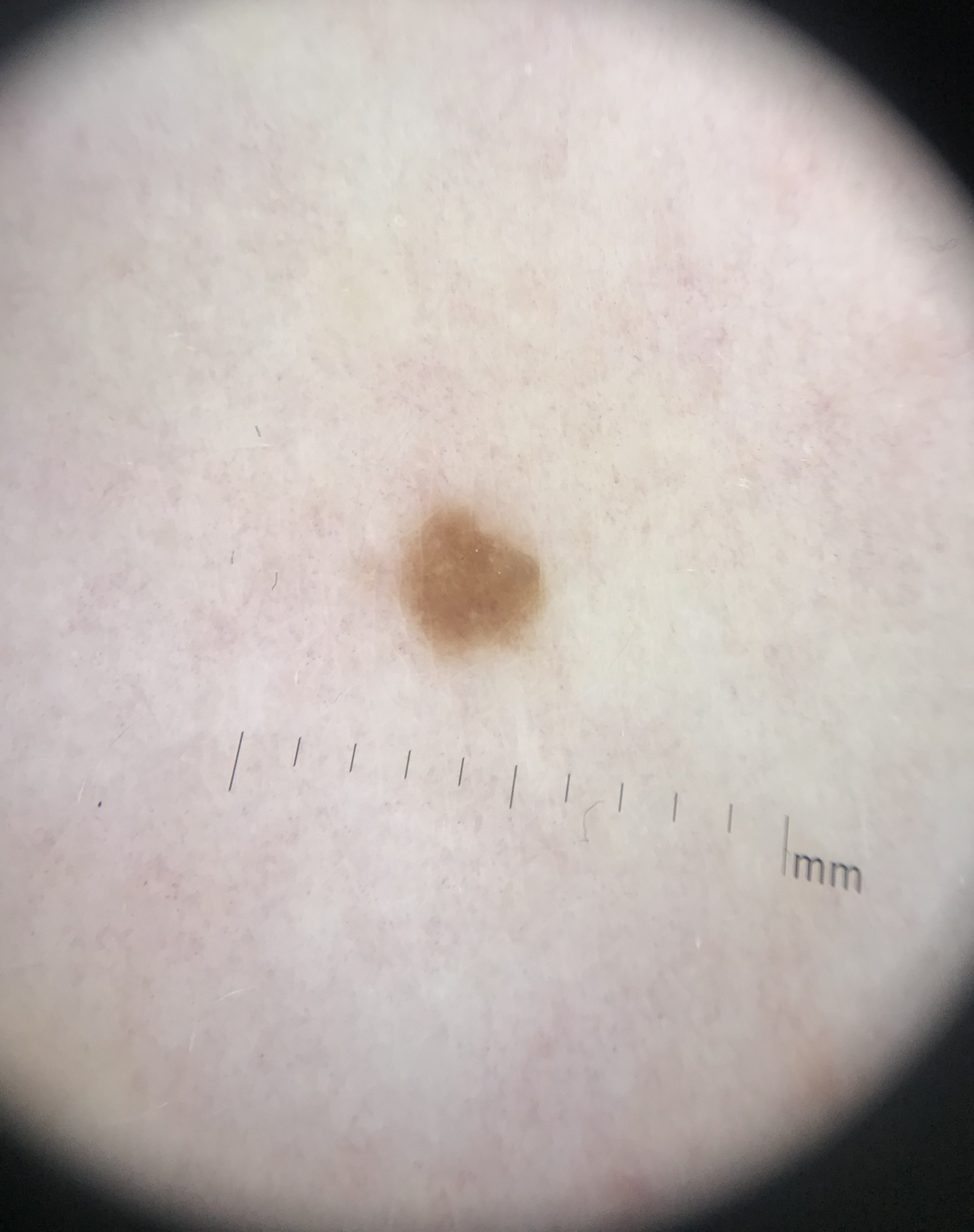A dermoscopic photograph of a skin lesion.
The morphology is that of a keratinocytic lesion.
The diagnostic label was a benign lesion — a seborrheic keratosis.